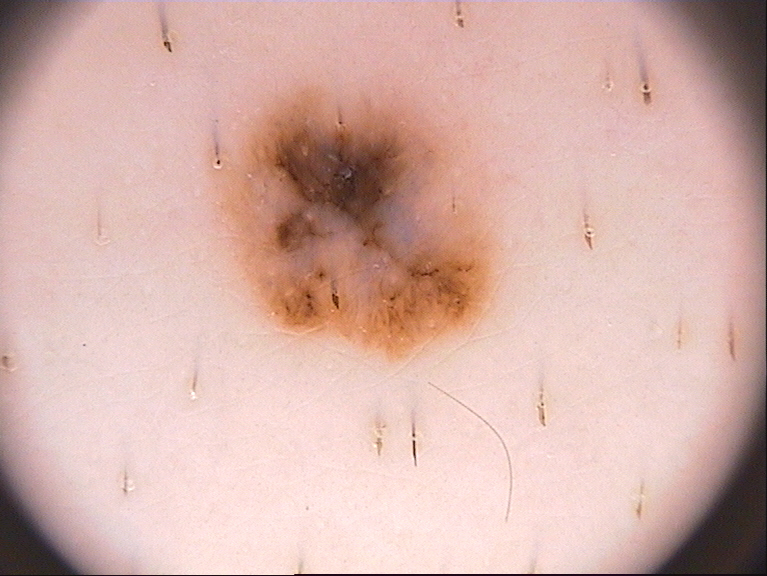The patient is a male aged 33 to 37.
Dermoscopy of a skin lesion.
Dermoscopically, the lesion shows no negative network, streaks, globules, milia-like cysts, or pigment network.
The lesion is located at x1=206 y1=75 x2=496 y2=358.
Consistent with a melanocytic nevus, a benign lesion.